The photo was captured at an angle; the patient is a female aged 70–79; located on the front of the torso and leg: 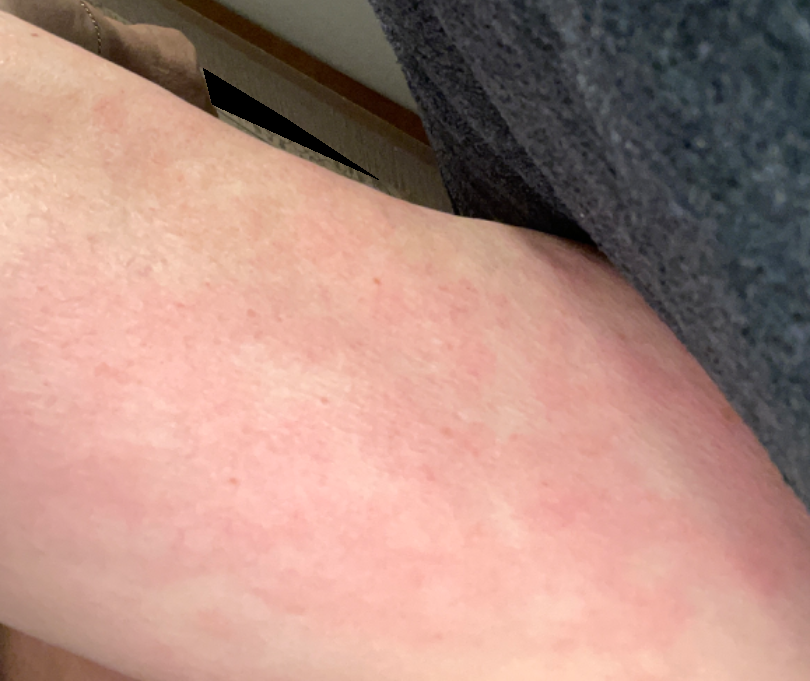Most consistent with Drug Rash; also consider Viral Exanthem; a more distant consideration is Urticaria.